The photograph was taken at an angle: 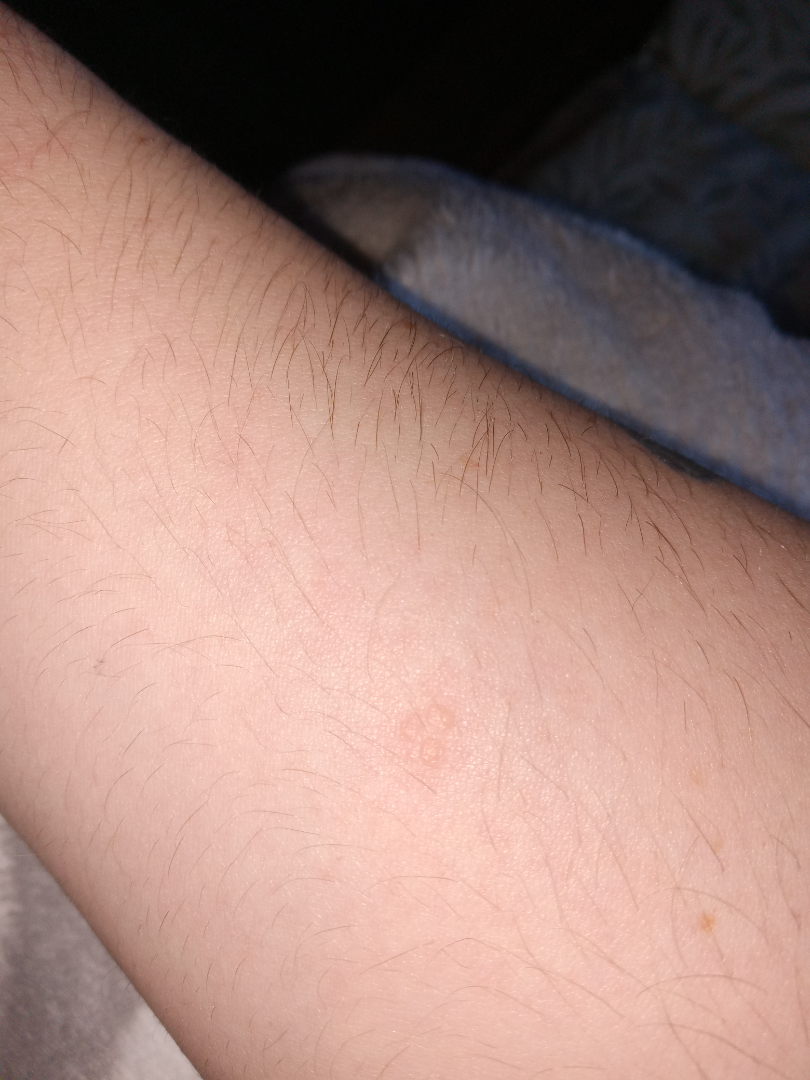On remote review of the image: the impression was split between Verruca vulgaris, Molluscum Contagiosum and Allergic Contact Dermatitis.